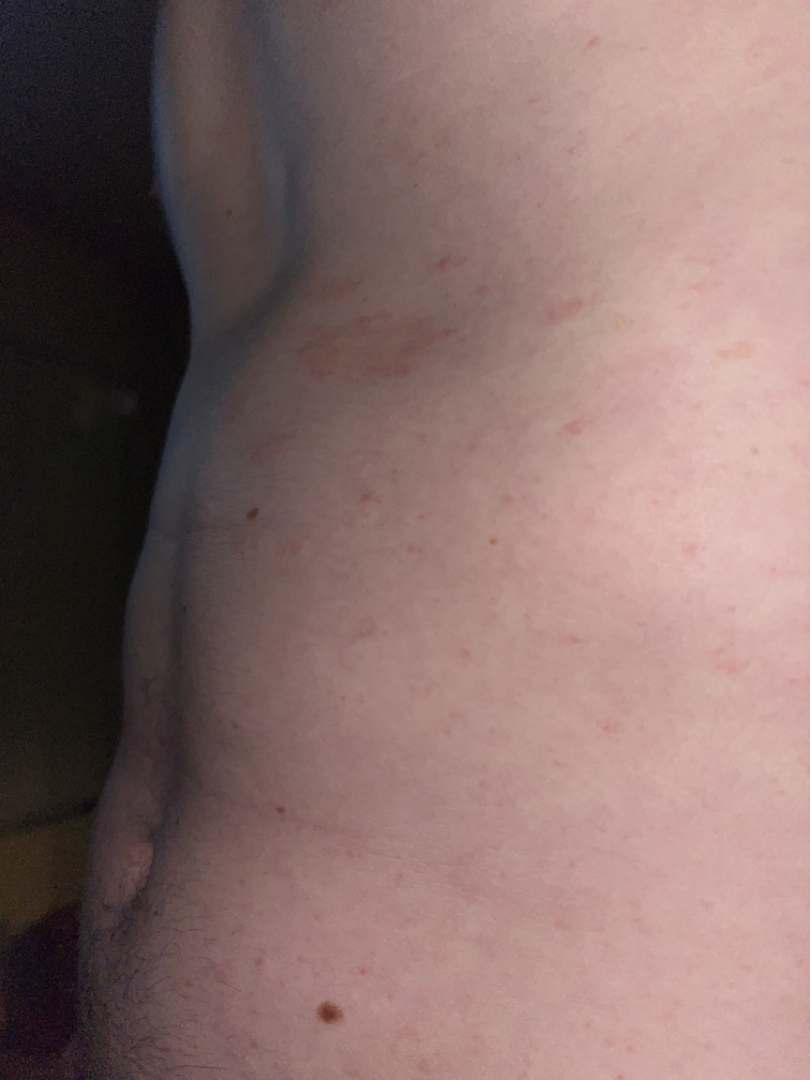Assessment: No differential diagnosis could be assigned on photographic review. Clinical context: The patient considered this a rash. An image taken at an angle. Texture is reported as raised or bumpy. The patient is a male aged 30–39. The lesion involves the back of the torso and front of the torso. The condition has been present for one to four weeks. The patient did not report lesion symptoms.